The photograph was taken at a distance, the patient considered this skin that appeared healthy to them, the arm is involved, reported duration is about one day, the lesion is associated with itching and enlargement, Fitzpatrick V; human graders estimated Monk Skin Tone 5 or 6, the patient indicates the lesion is raised or bumpy, no constitutional symptoms were reported — 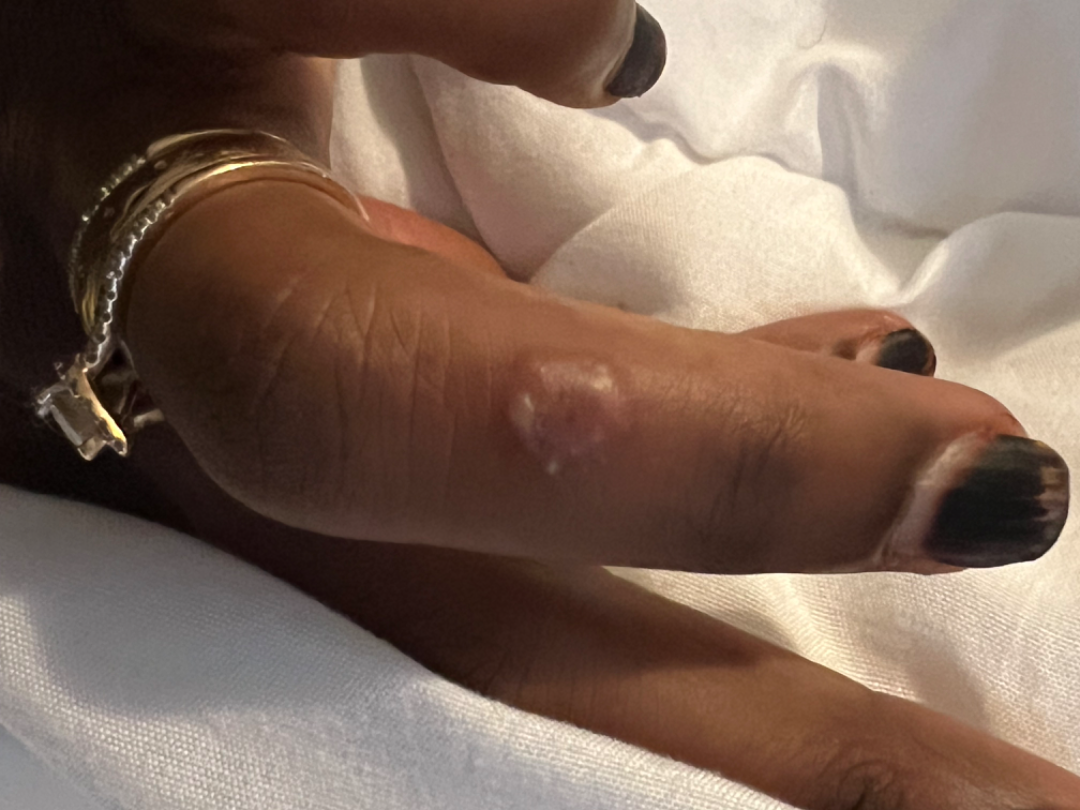Q: What was the assessment?
A: unable to determine